Dermoscopy of a skin lesion; a male subject aged 28 to 32:
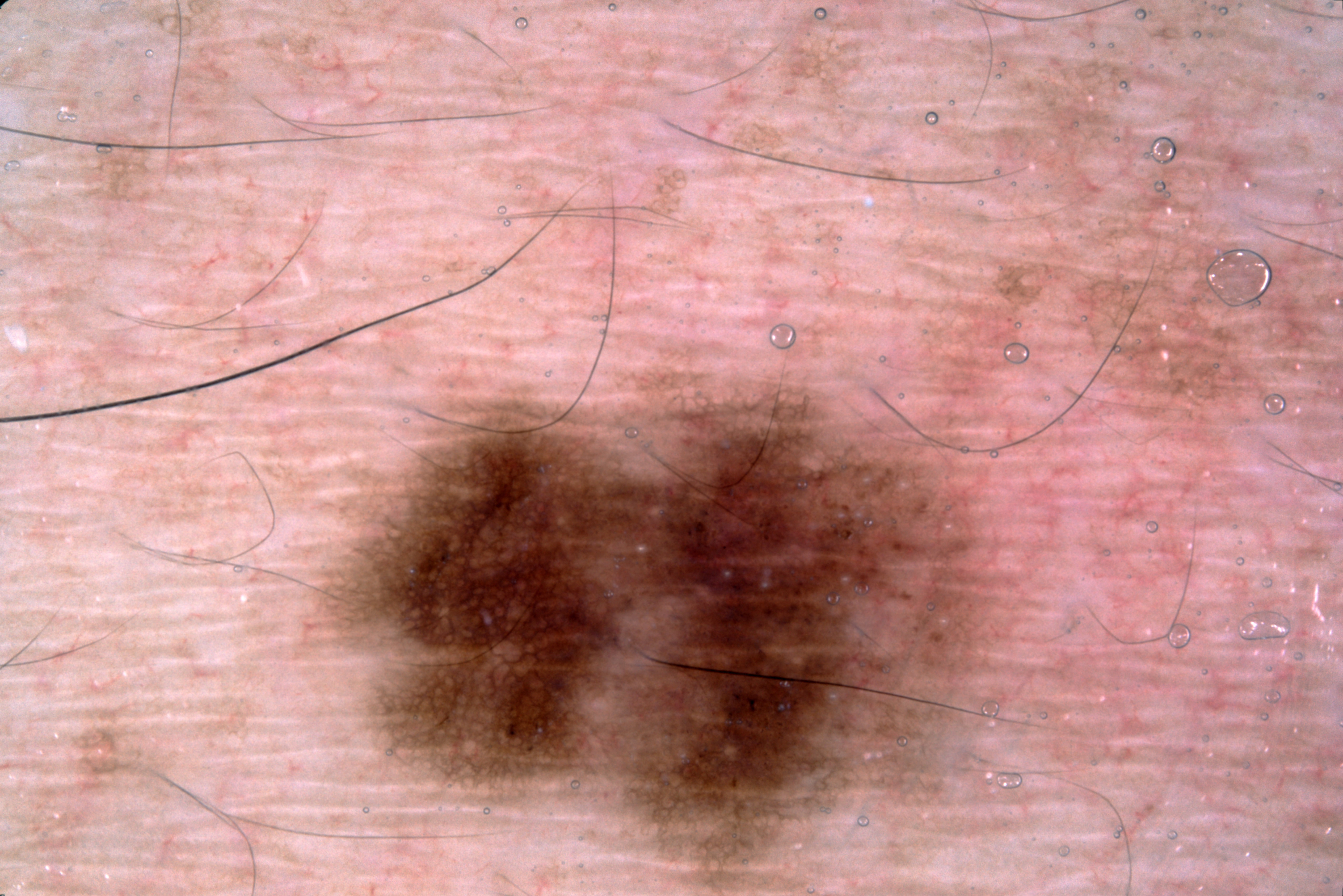Case summary:
On dermoscopy, the lesion shows milia-like cysts and pigment network; no streaks or negative network. As (left, top, right, bottom), the lesion spans [322, 383, 1001, 892].
Conclusion:
The diagnostic assessment was a melanocytic nevus, a benign lesion.